A clinical photograph of a skin lesion · the patient was assessed as skin type III · the chart records prior malignancy (patient or family) · a female patient 73 years old — 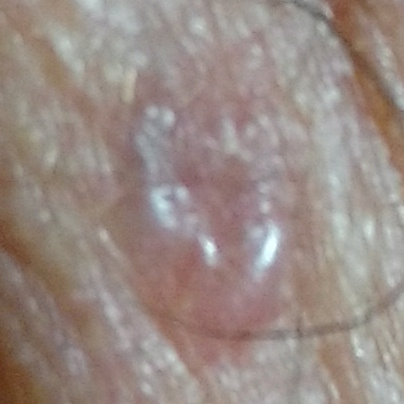Findings:
The lesion is located on the face. The lesion is roughly 6 by 6 mm. By the patient's account, the lesion is elevated.
Conclusion:
Histopathological examination showed a basal cell carcinoma.